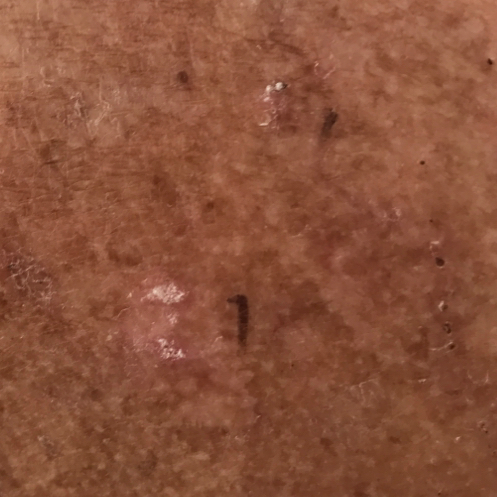Case:
• modality: clinical photograph
• site: the chest
• reported symptoms: itching
• impression: actinic keratosis (clinical consensus)